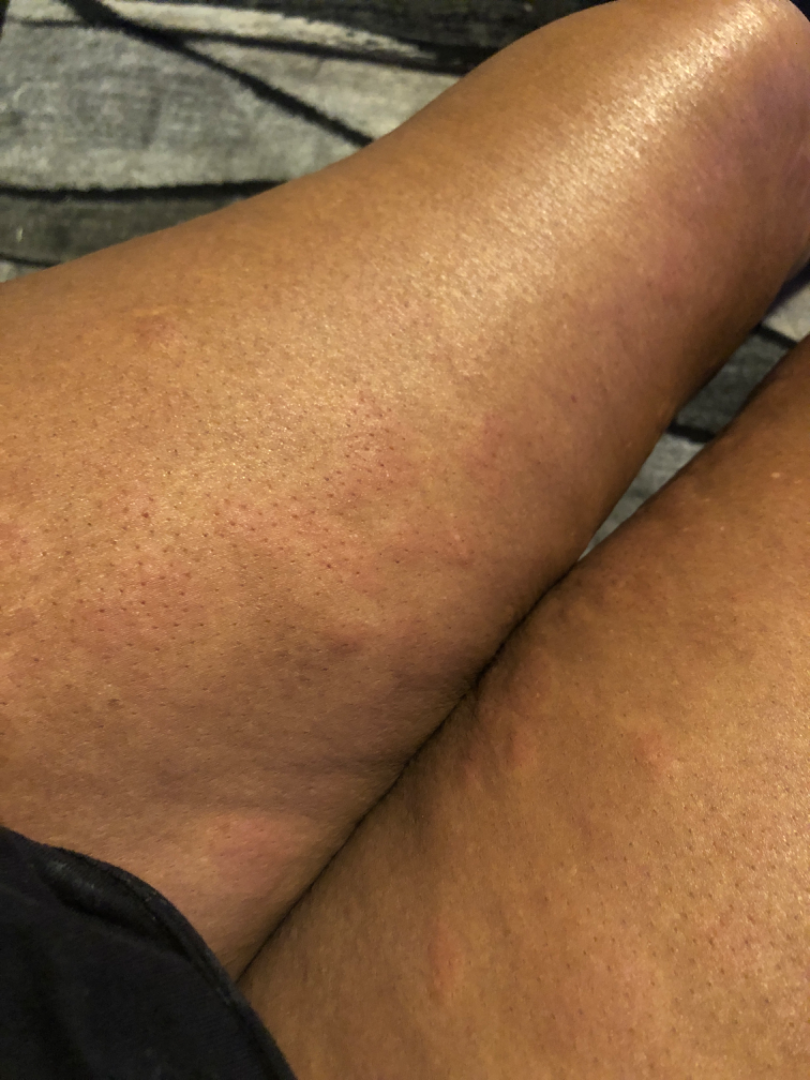Background: The patient indicates itching. The patient is a female aged 60–69. The patient indicates the condition has been present for three to twelve months. The patient indicates the lesion is raised or bumpy. The lesion involves the palm, head or neck, front of the torso and arm. A close-up photograph. Self-categorized by the patient as a rash. Findings: The reviewing dermatologist's impression was: Urticaria (favored).